A dermoscopic close-up of a skin lesion.
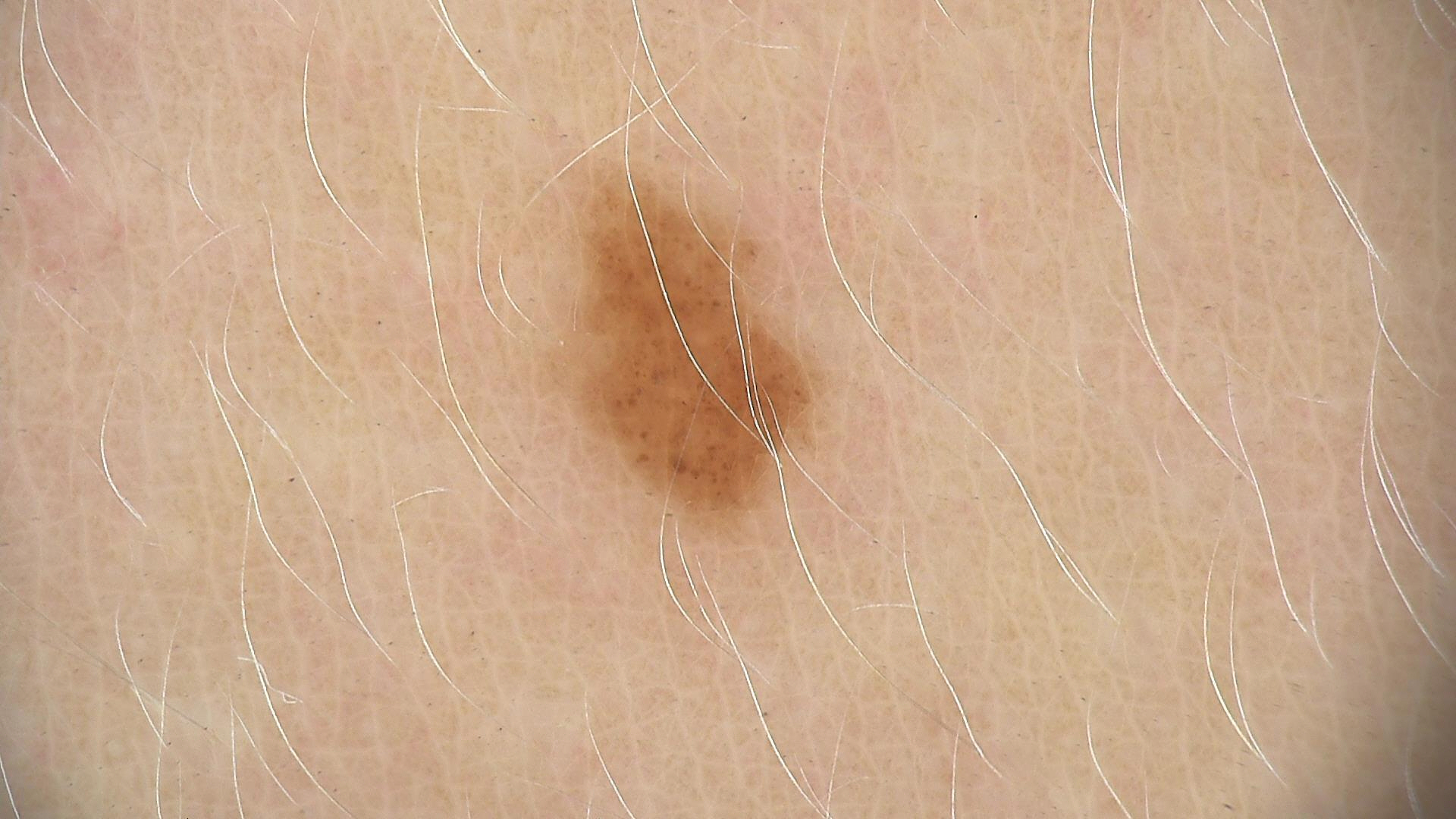Conclusion: Consistent with a dysplastic junctional nevus.